Present for one to four weeks · the lesion is associated with itching · the affected area is the arm · female patient, age 50–59 · self-categorized by the patient as a rash · texture is reported as raised or bumpy and rough or flaky · this image was taken at a distance.
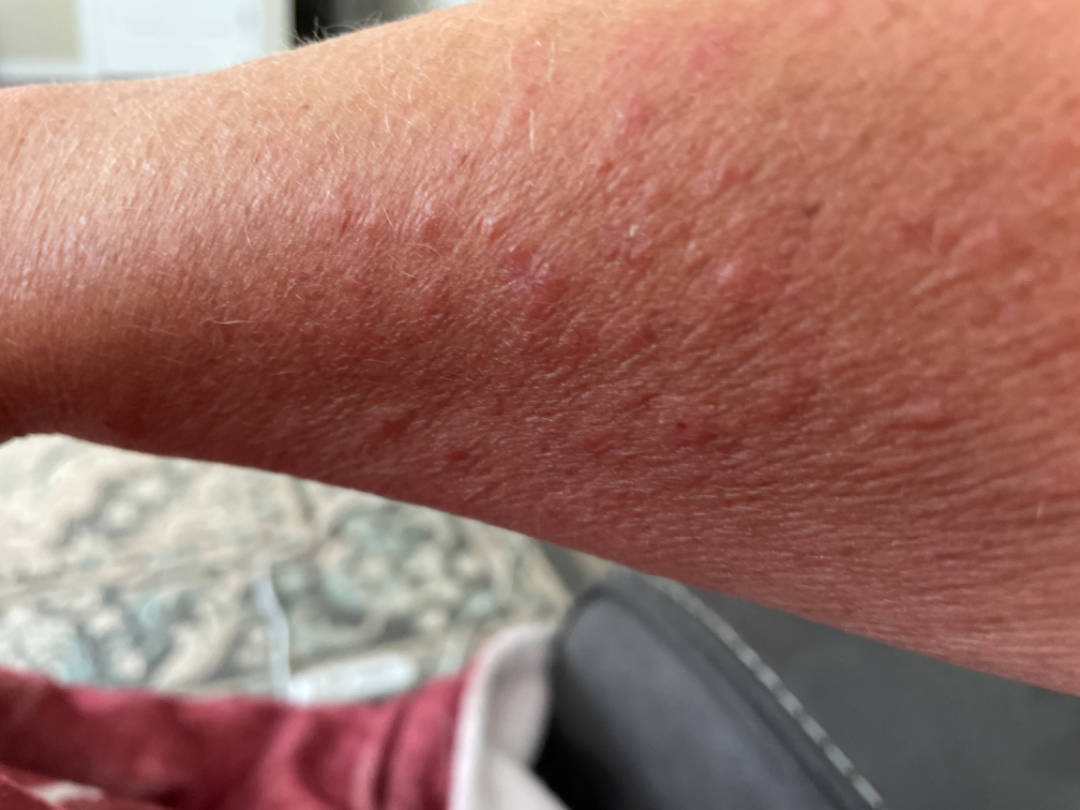  assessment: unable to determine